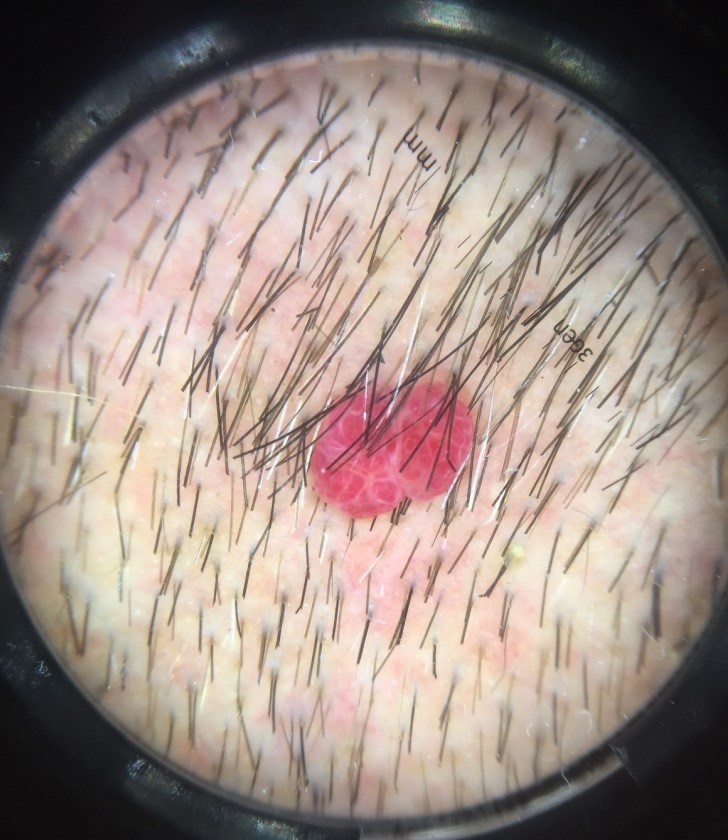Dermoscopy of a skin lesion. The diagnostic label was a vascular, benign lesion — a hemangioma.